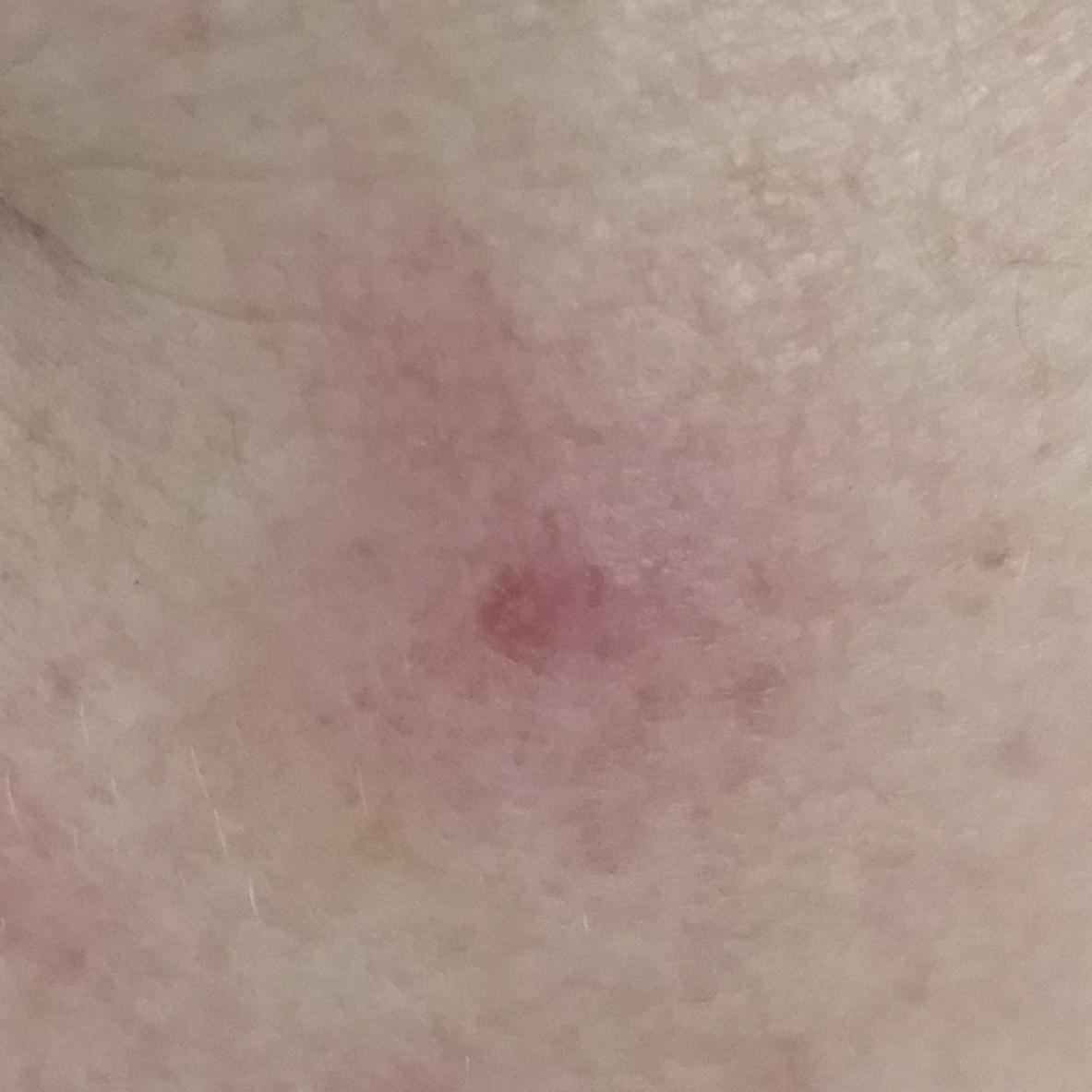A smartphone photograph of a skin lesion. A patient aged 55. Located on the face. The patient describes that the lesion itches. Diagnosed by dermatologist consensus as an actinic keratosis.